An image taken at an angle:
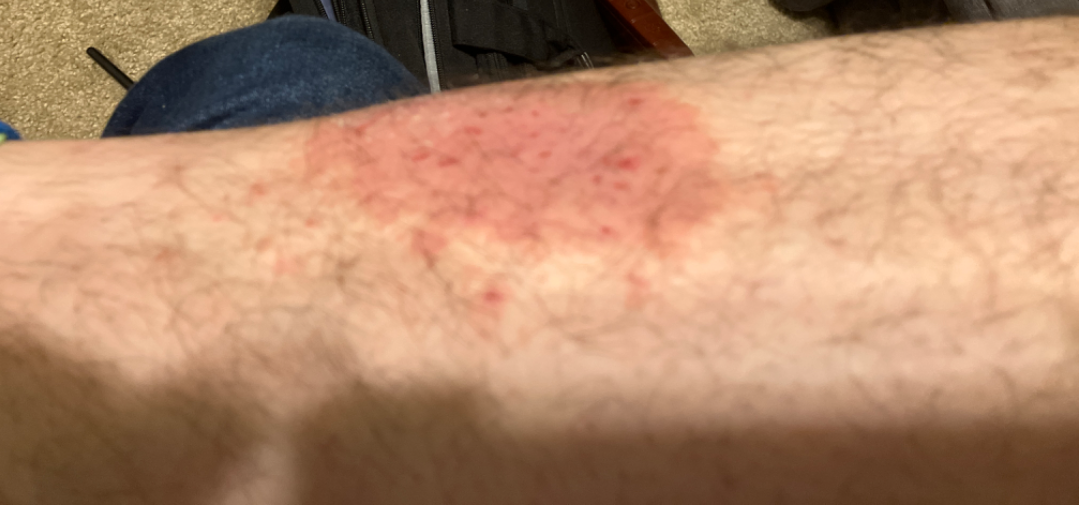The image was not sufficient for the reviewer to characterize the skin condition. Fitzpatrick III.